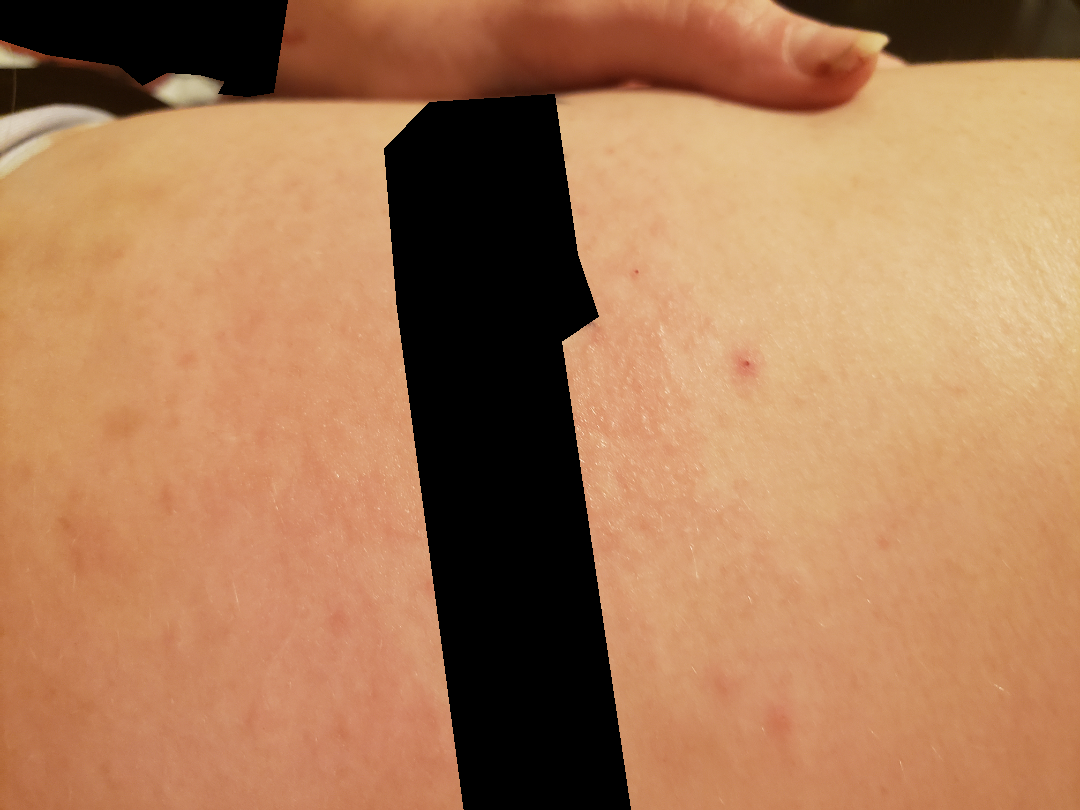{"symptoms": ["itching", "bothersome appearance"], "patient": "female, age 30–39", "body_site": "leg", "shot_type": "at an angle", "duration": "one to four weeks", "systemic_symptoms": "none reported", "patient_category": "a rash", "differential": {"Allergic Contact Dermatitis": 0.52, "Folliculitis": 0.26, "Urticaria": 0.11, "Eczema": 0.11}}